A dermoscopy image of a single skin lesion:
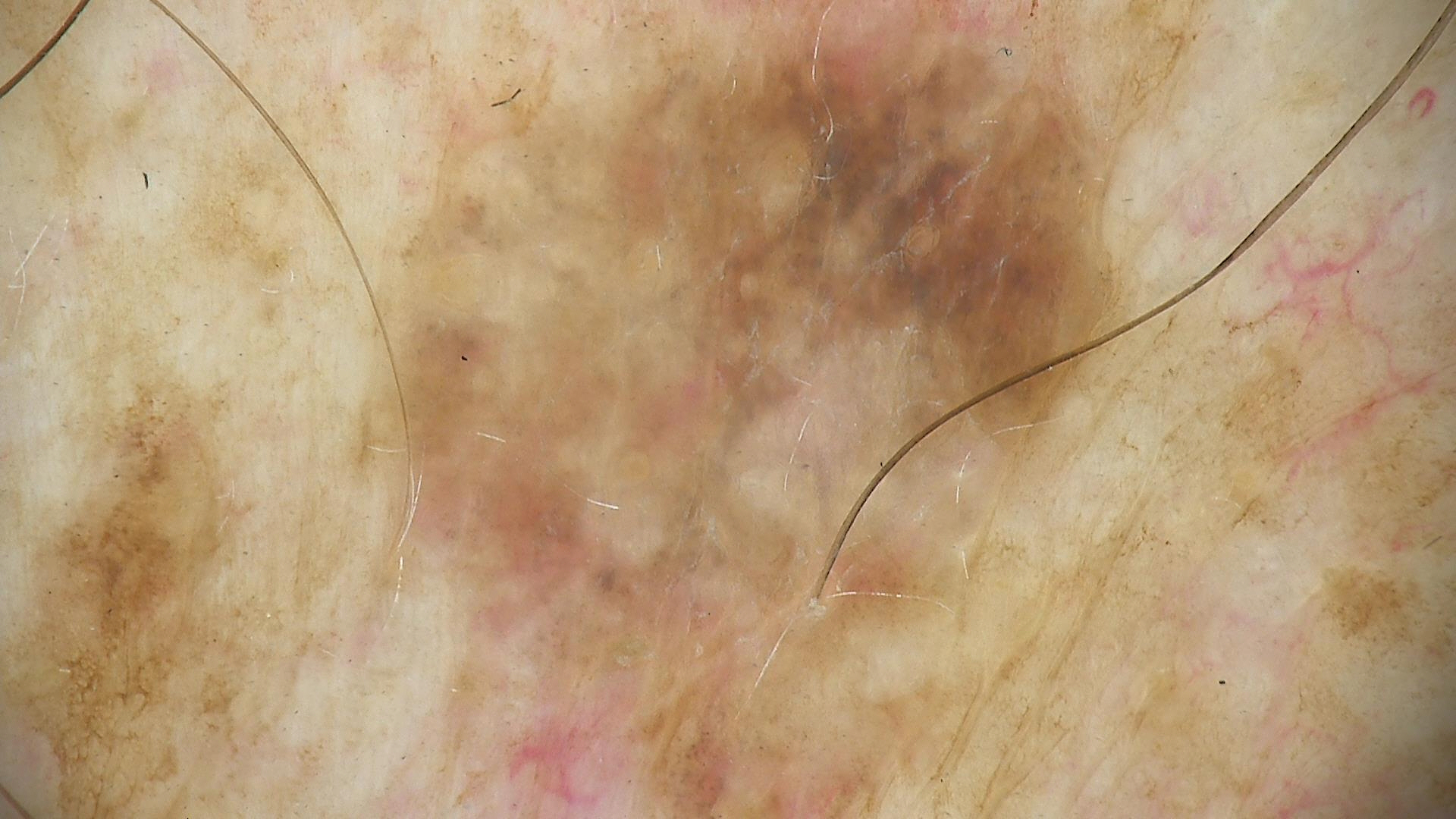Q: What was the diagnostic impression?
A: dysplastic junctional nevus (expert consensus)